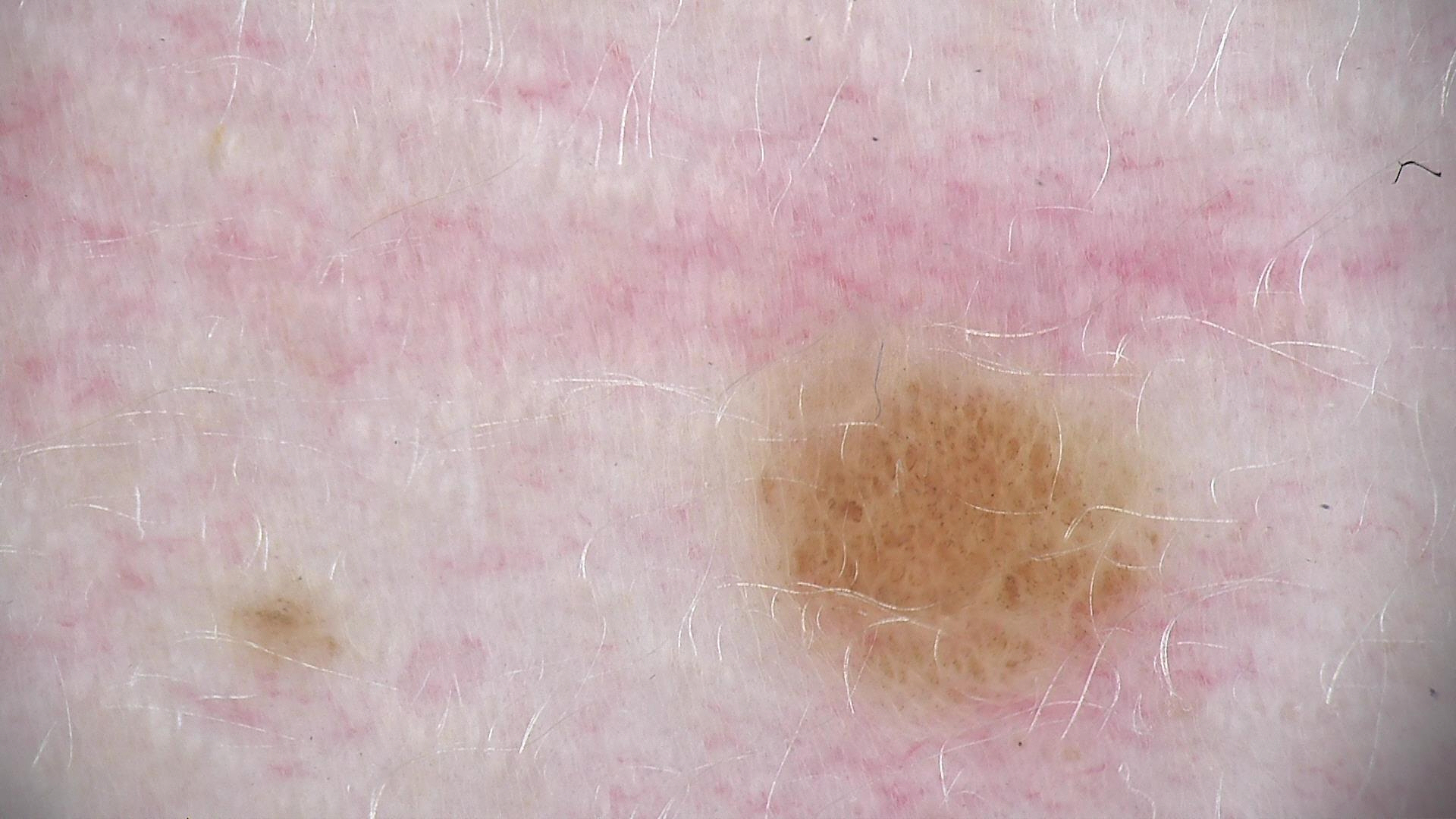<case>
  <image>dermatoscopy</image>
  <lesion_type>
    <main_class>banal</main_class>
    <pattern>compound</pattern>
  </lesion_type>
  <diagnosis>
    <name>compound nevus</name>
    <code>cb</code>
    <malignancy>benign</malignancy>
    <super_class>melanocytic</super_class>
    <confirmation>expert consensus</confirmation>
  </diagnosis>
</case>